The photograph is a close-up of the affected area.
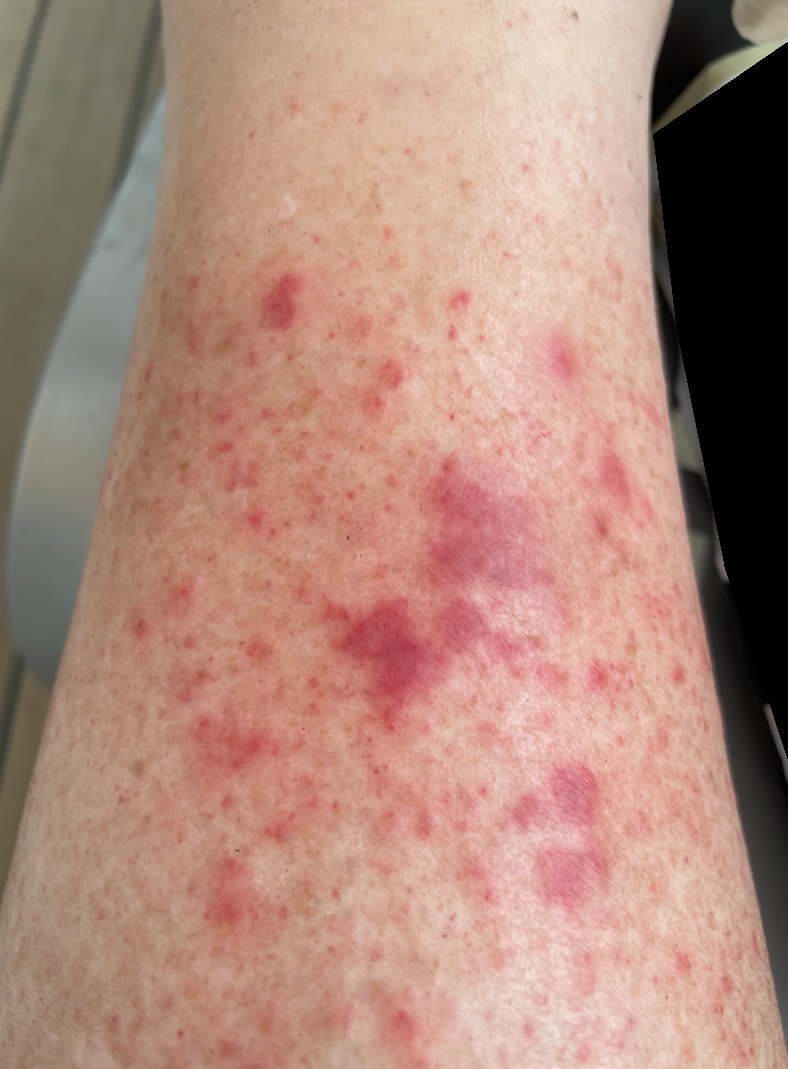{"differential": {"leading": ["Leukocytoclastic Vasculitis"], "considered": ["Eczema"]}}